An image taken at a distance.
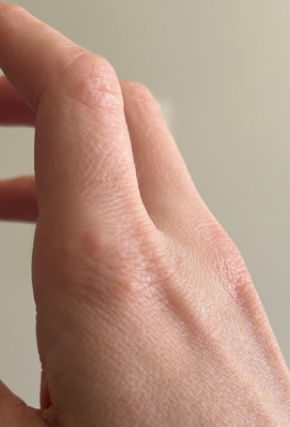<dermatology_case>
  <differential>
    <leading>Insect Bite</leading>
    <considered>Urticaria, Allergic Contact Dermatitis</considered>
  </differential>
</dermatology_case>